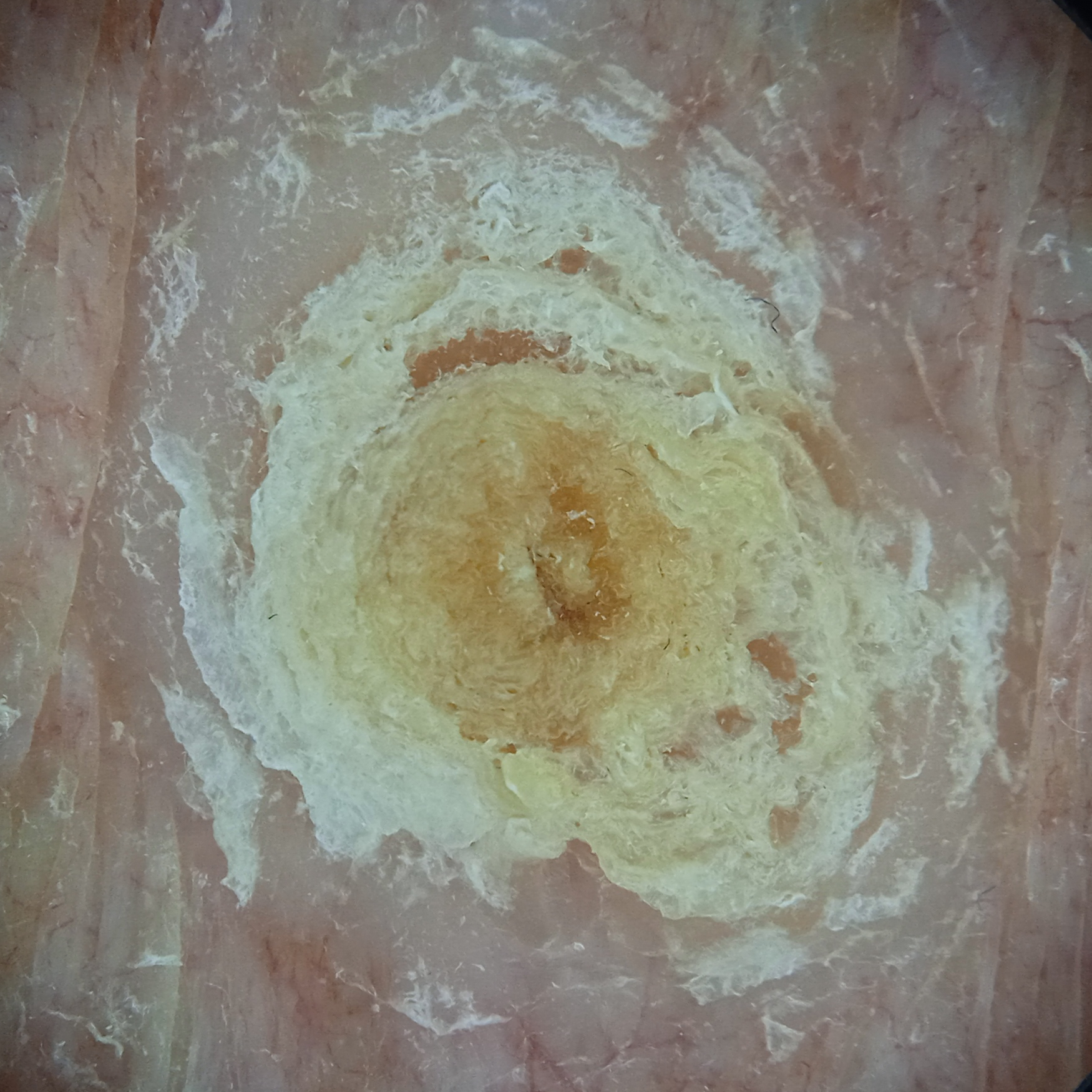patient = female, 92 years old | sun reaction = skin tans without first burning | referral context = research study (no referral diagnosis) | imaging = dermatoscopic image | relevant history = a personal history of cancer, a family history of skin cancer | body site = the torso | size = 12.5 mm | diagnosis = squamous cell carcinoma (dermatologist consensus).